A skin lesion imaged with a dermatoscope: 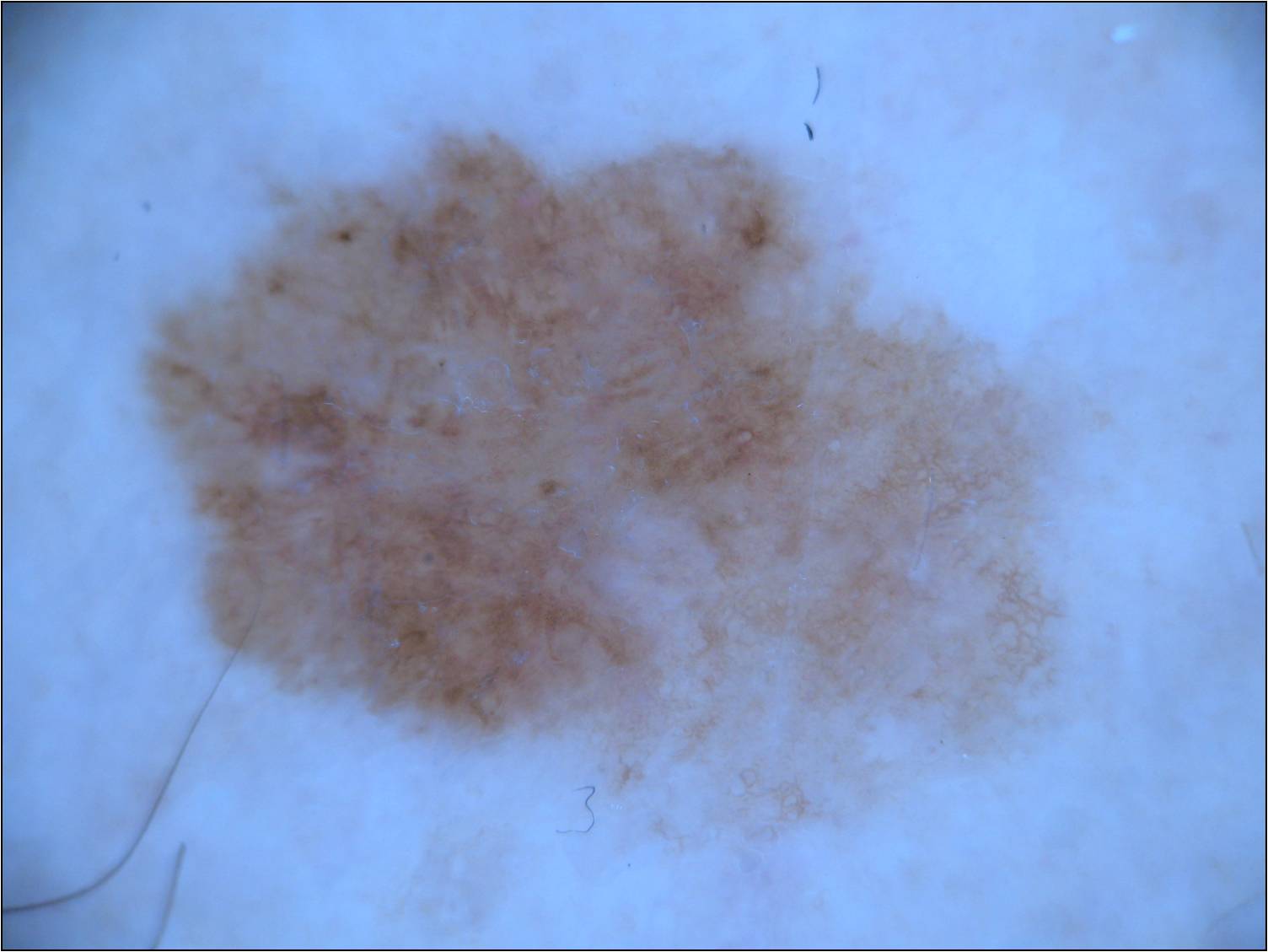Findings: A large lesion occupying much of the field. Dermoscopically, the lesion shows pigment network and globules. Lesion location: x1=133 y1=126 x2=1061 y2=820. Diagnosis: Histopathologically confirmed as a melanoma.